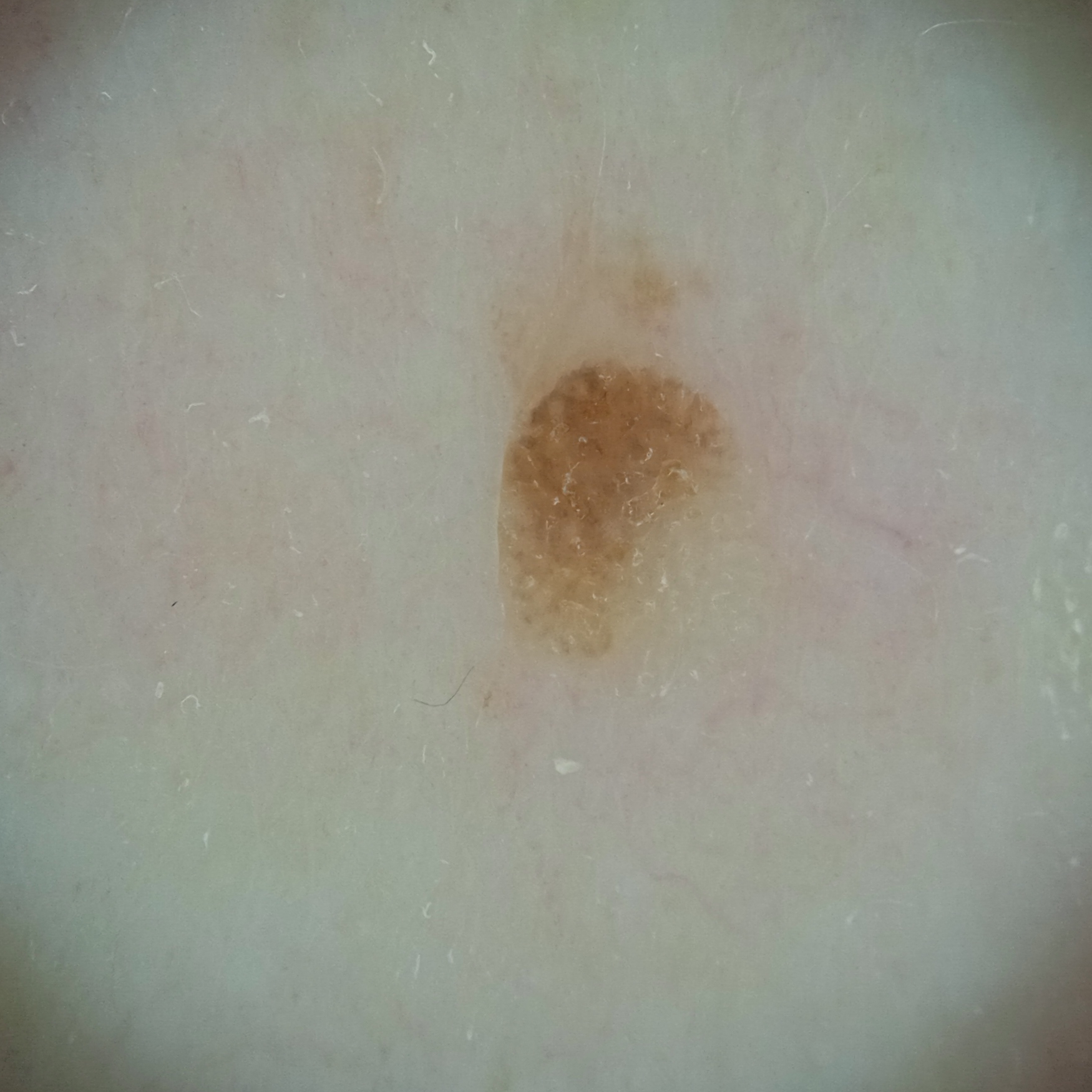assessment=seborrheic keratosis (dermatologist consensus).